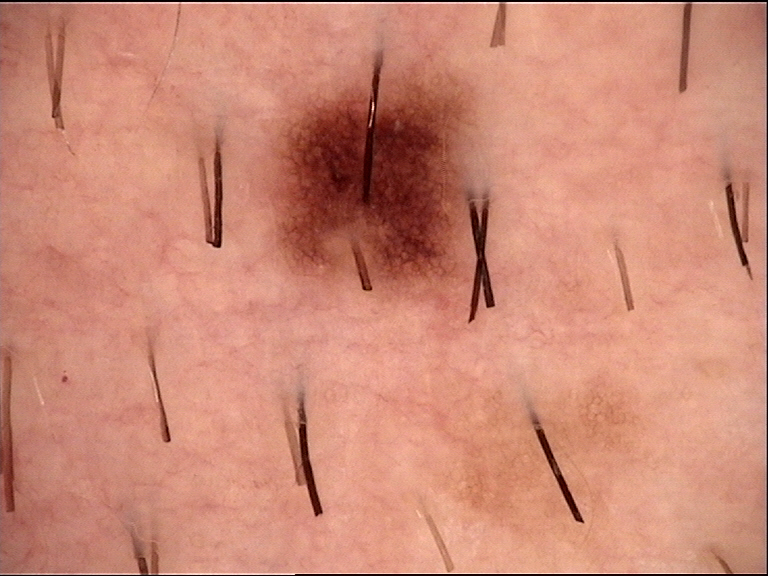| feature | finding |
|---|---|
| label | dysplastic junctional nevus (expert consensus) |